Dermoscopy of a skin lesion.
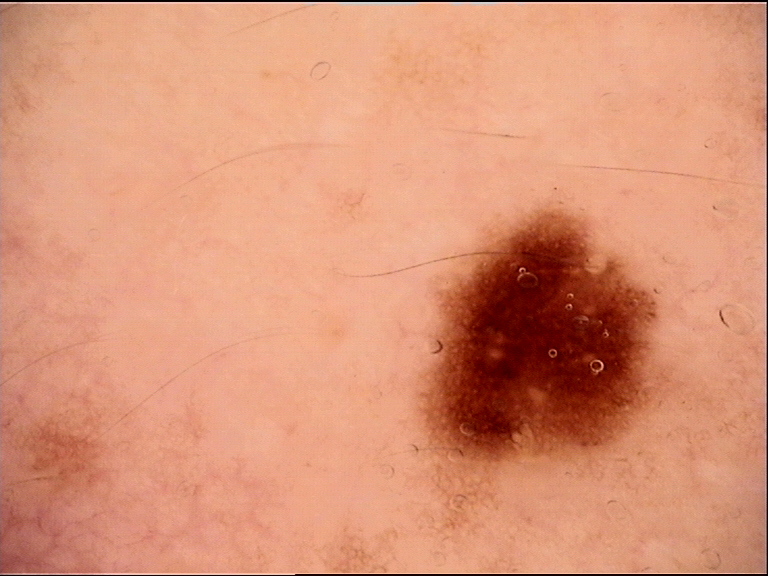Labeled as a benign lesion — a dysplastic junctional nevus.